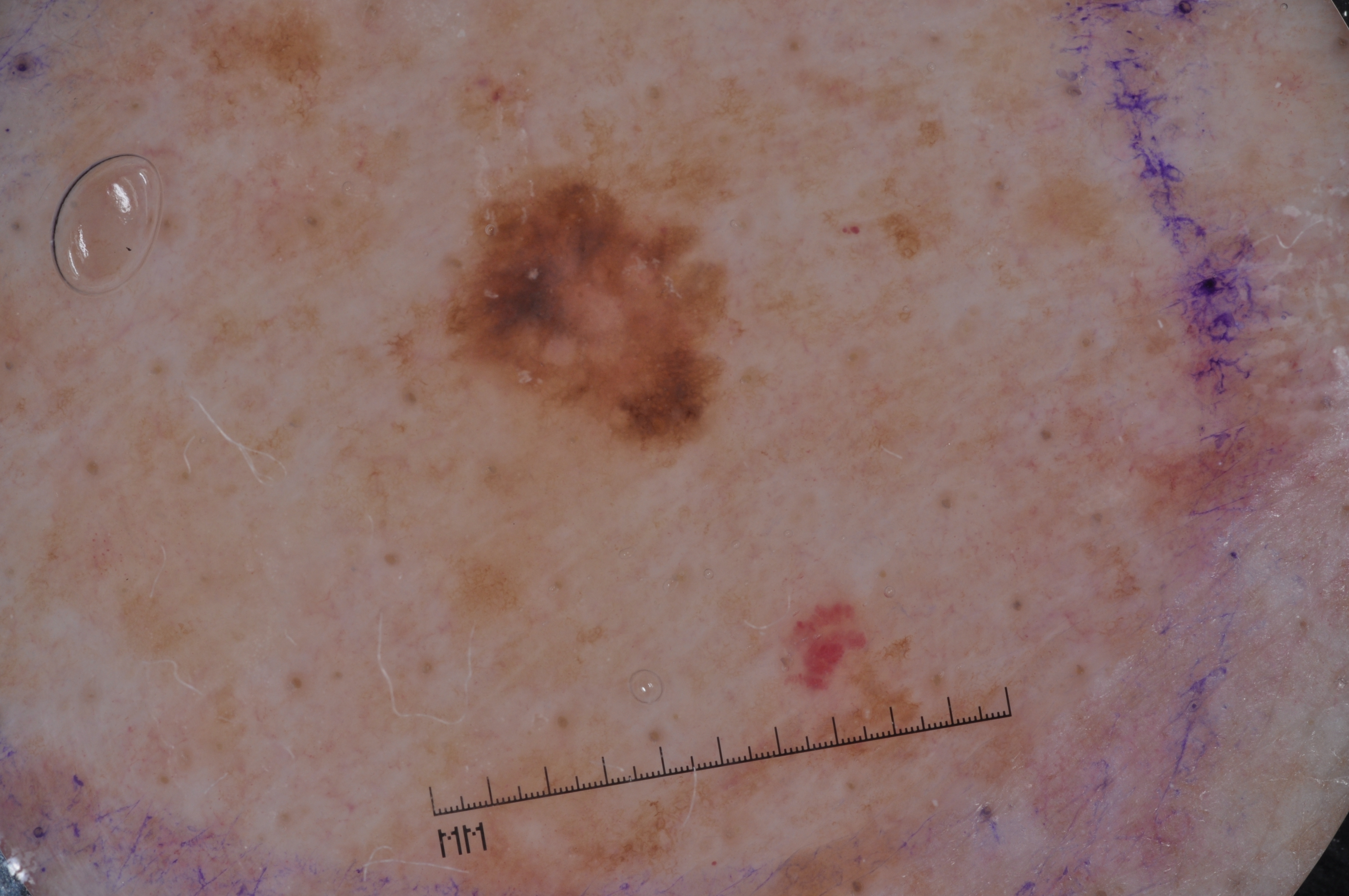{"patient": {"sex": "male", "age_approx": 65}, "image": {"modality": "dermoscopy"}, "dermoscopic_features": {"present": ["milia-like cysts", "pigment network"], "absent": ["streaks", "negative network"]}, "lesion_extent": "small", "lesion_location": {"bbox_xyxy": [443, 168, 727, 448]}, "diagnosis": {"name": "melanoma", "malignancy": "malignant", "lineage": "melanocytic", "provenance": "histopathology"}}